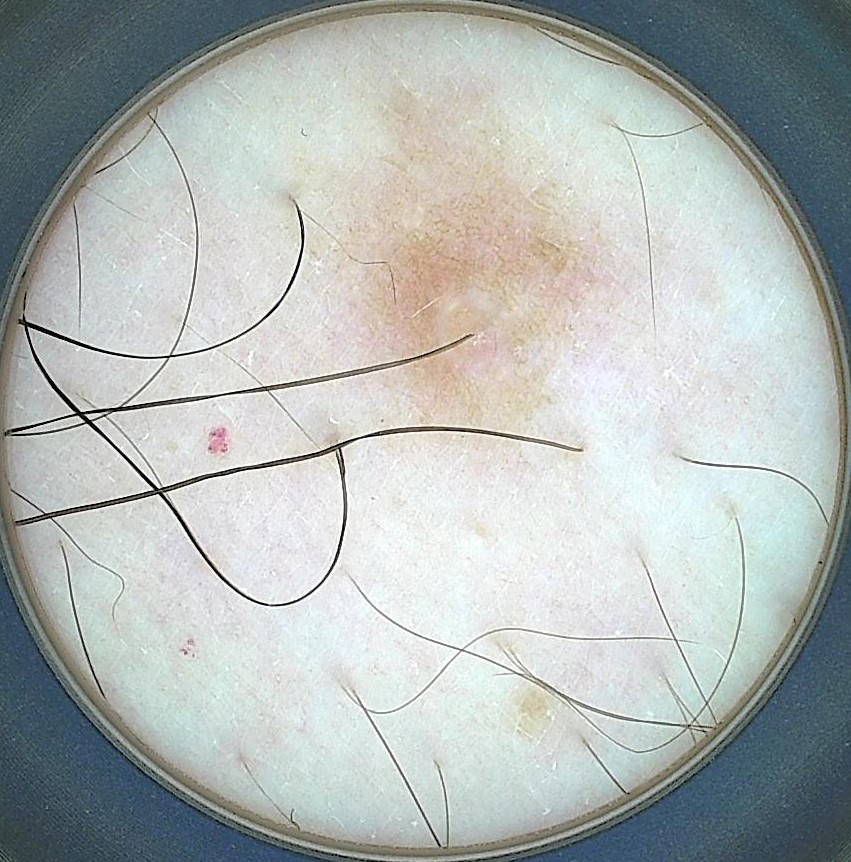A skin lesion imaged with a dermatoscope. The architecture is that of a banal lesion. Consistent with a junctional nevus.